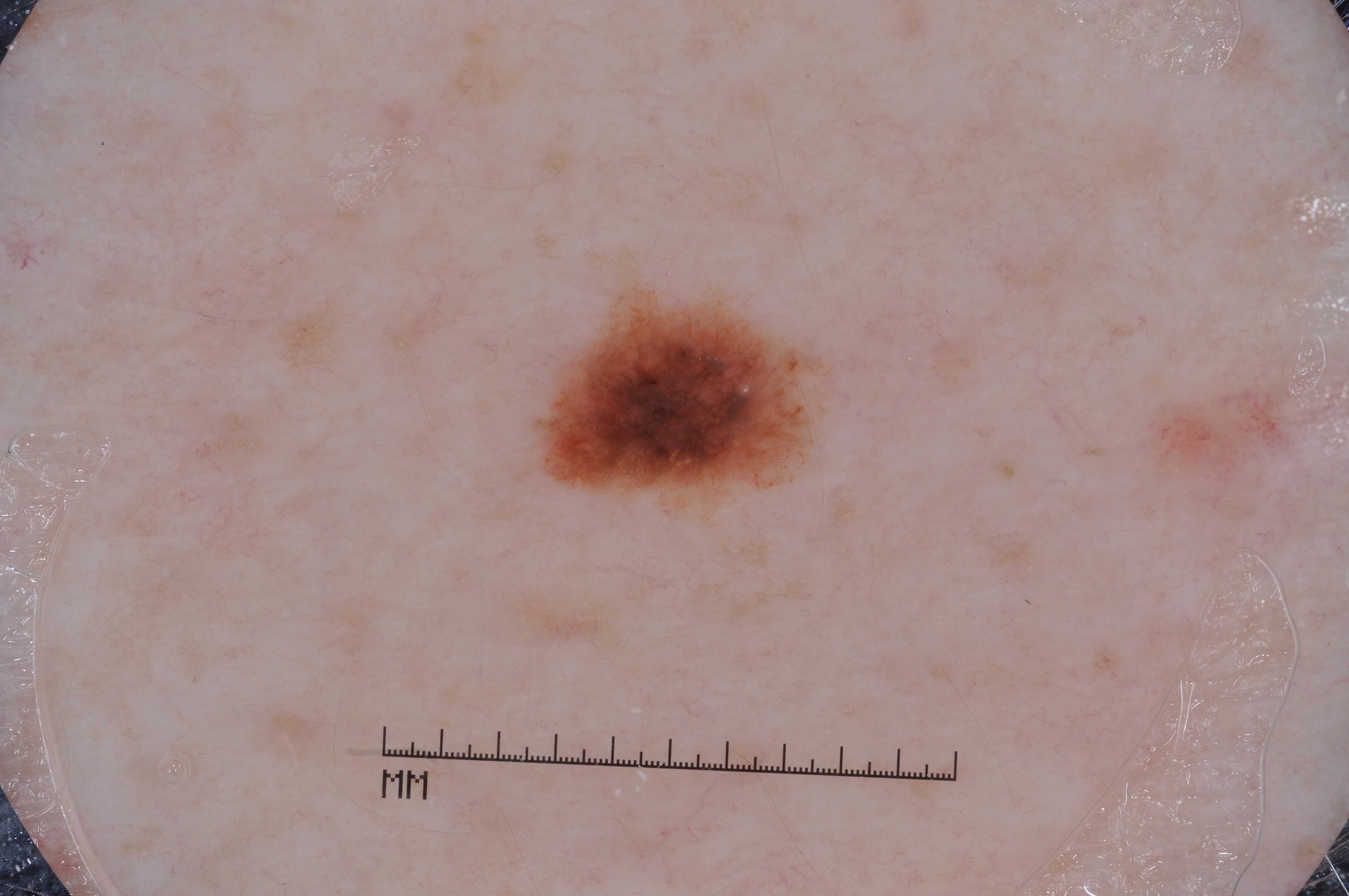Notes:
• modality: dermoscopy of a skin lesion
• patient: male, in their mid- to late 60s
• features: milia-like cysts and pigment network
• lesion location: x1=538 y1=301 x2=811 y2=497
• extent: ~3% of the field
• diagnostic label: a melanocytic nevus